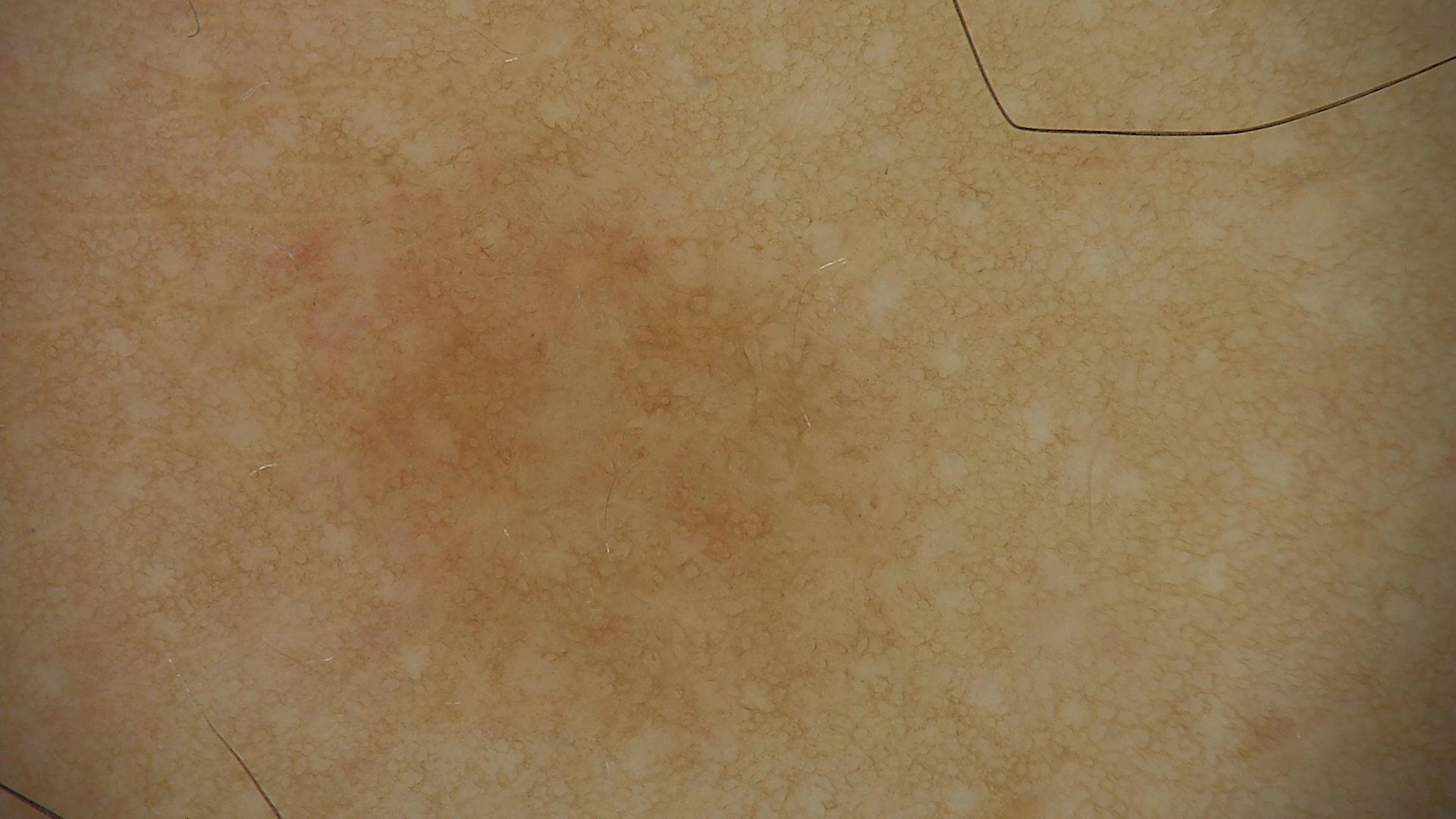Classified as a solar lentigo.